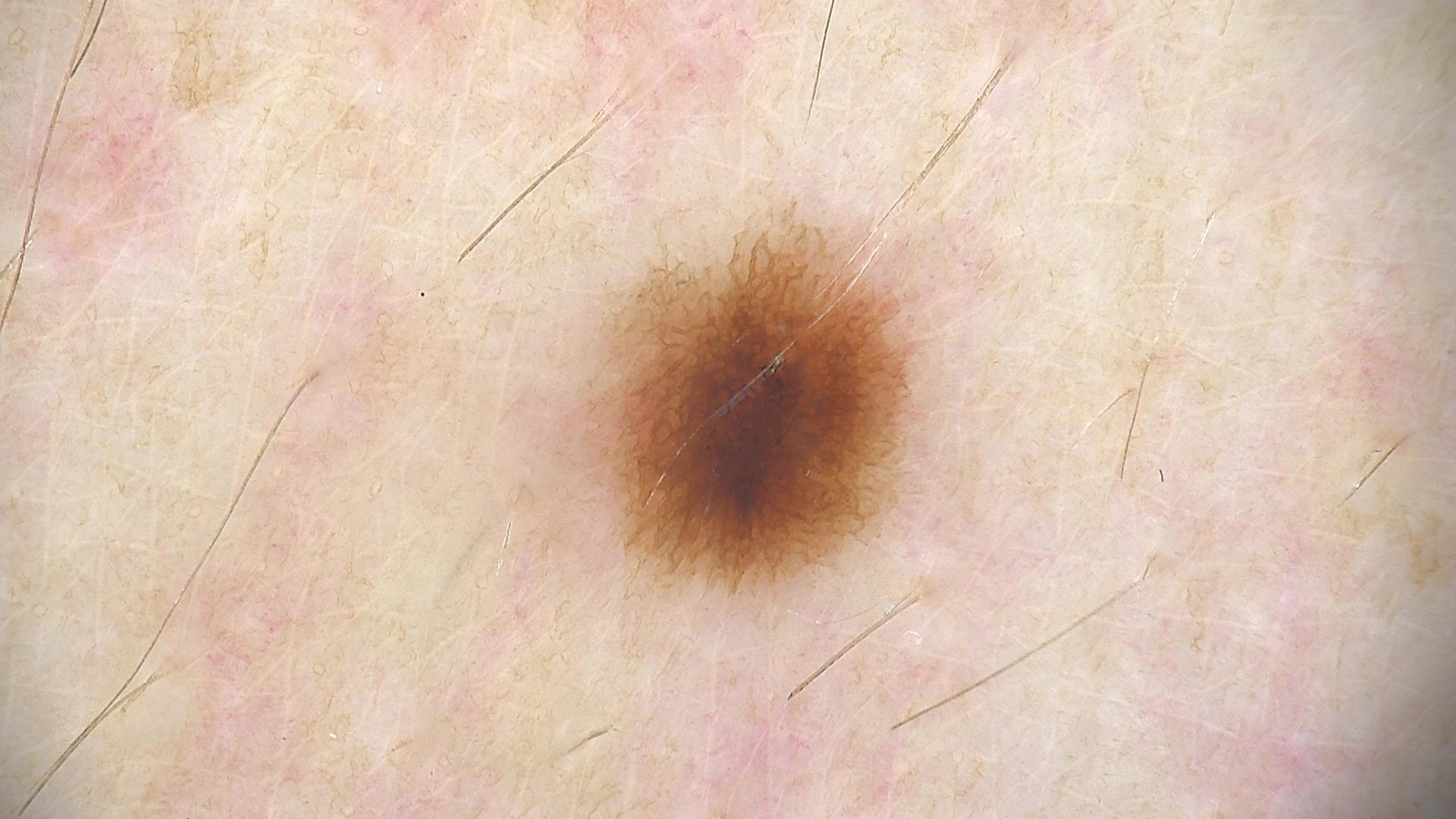The diagnostic label was a dysplastic junctional nevus.